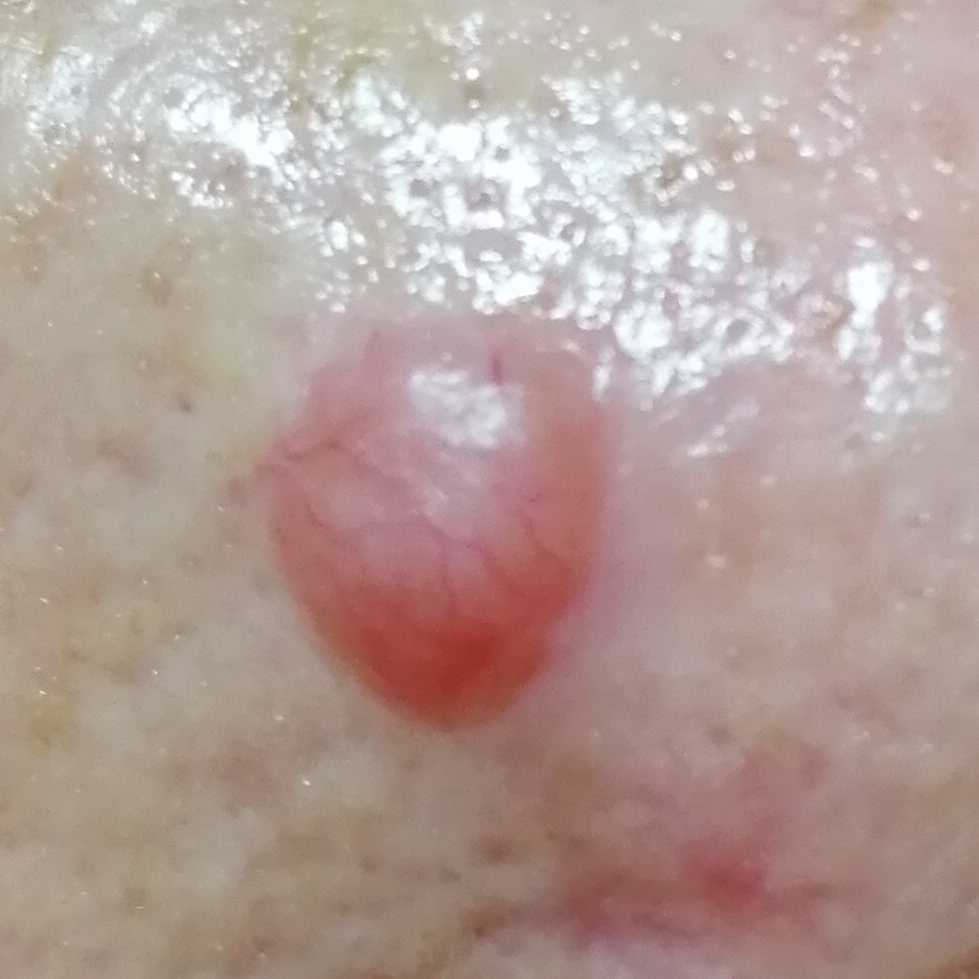Skin type II. A female subject age 65. The lesion was found on the nose. Measuring about 9 × 7 mm. The patient reports that the lesion is elevated, but does not itch. Histopathological examination showed a basal cell carcinoma.